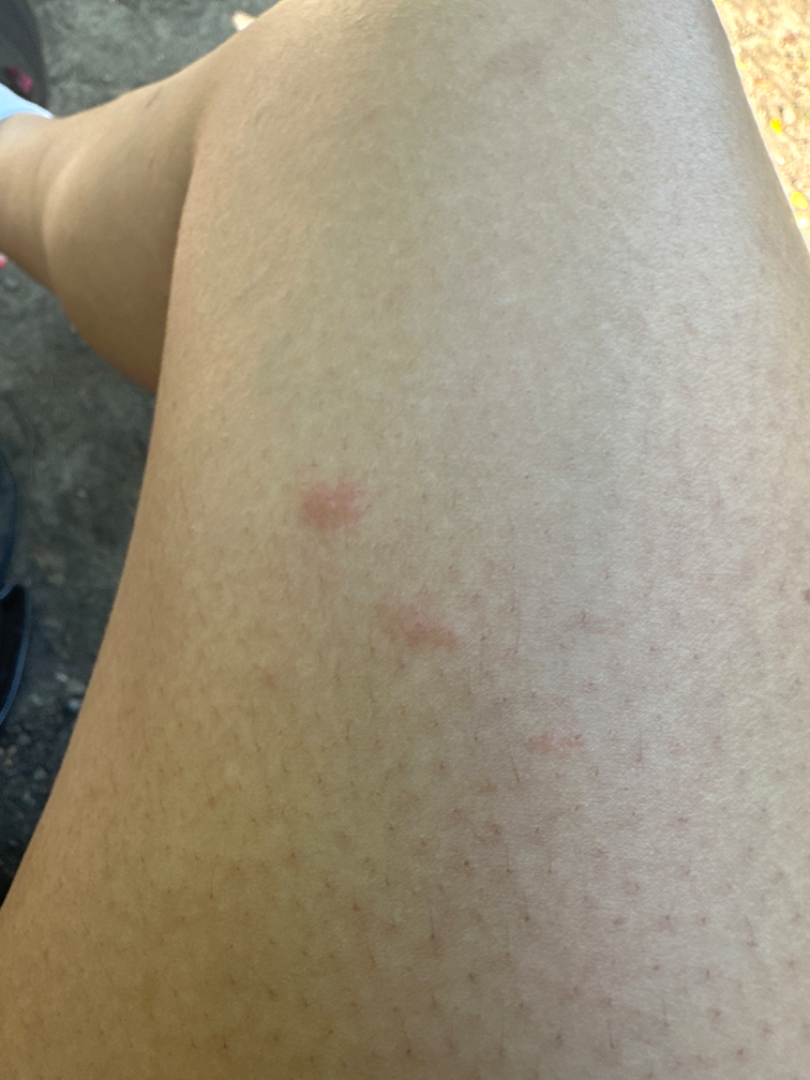The leading impression is Insect Bite; the differential also includes Allergic Contact Dermatitis; a remote consideration is Urticaria.